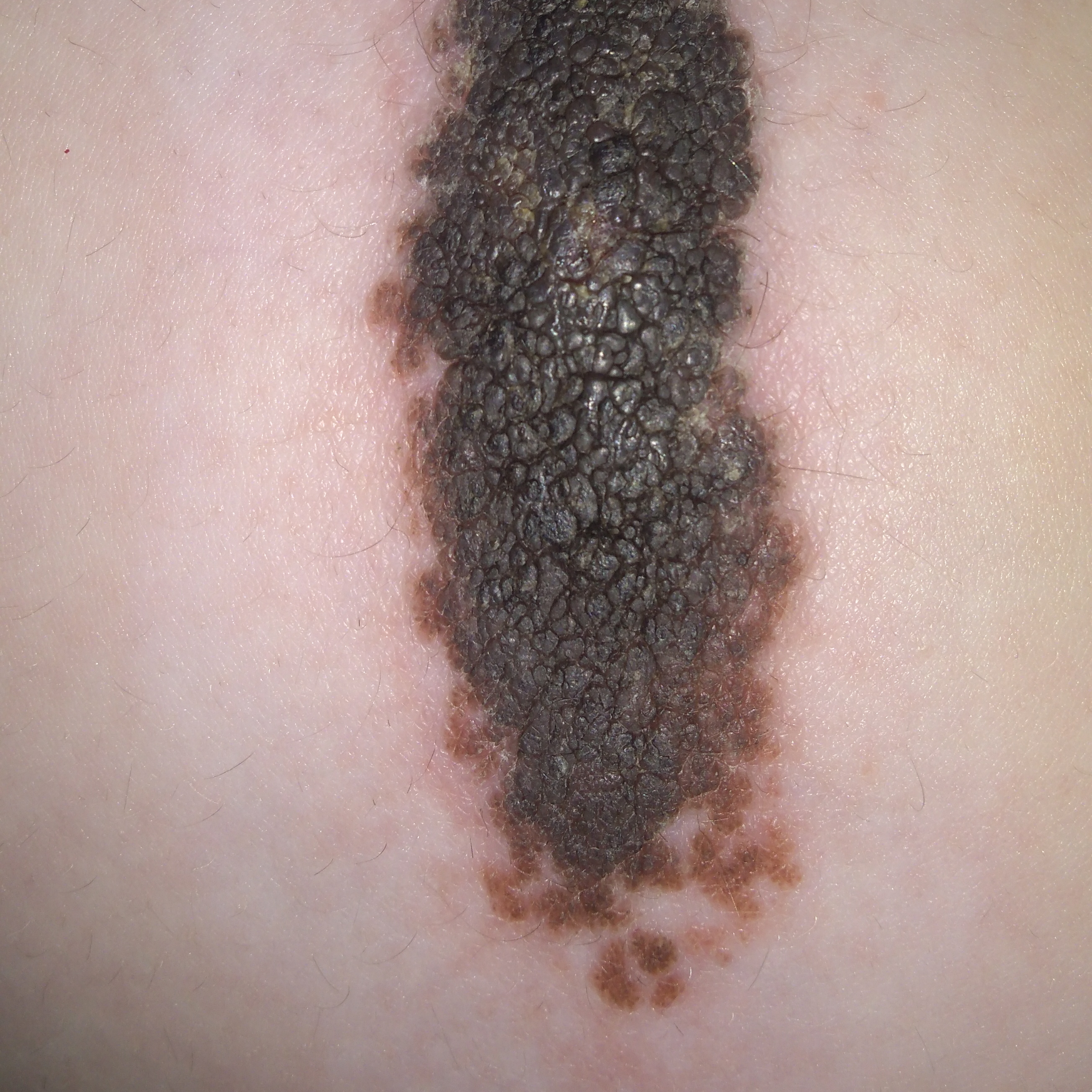Q: What is this lesion?
A: nevus (biopsy-proven)